The leg is involved. Male patient, age 18–29. This is a close-up image: 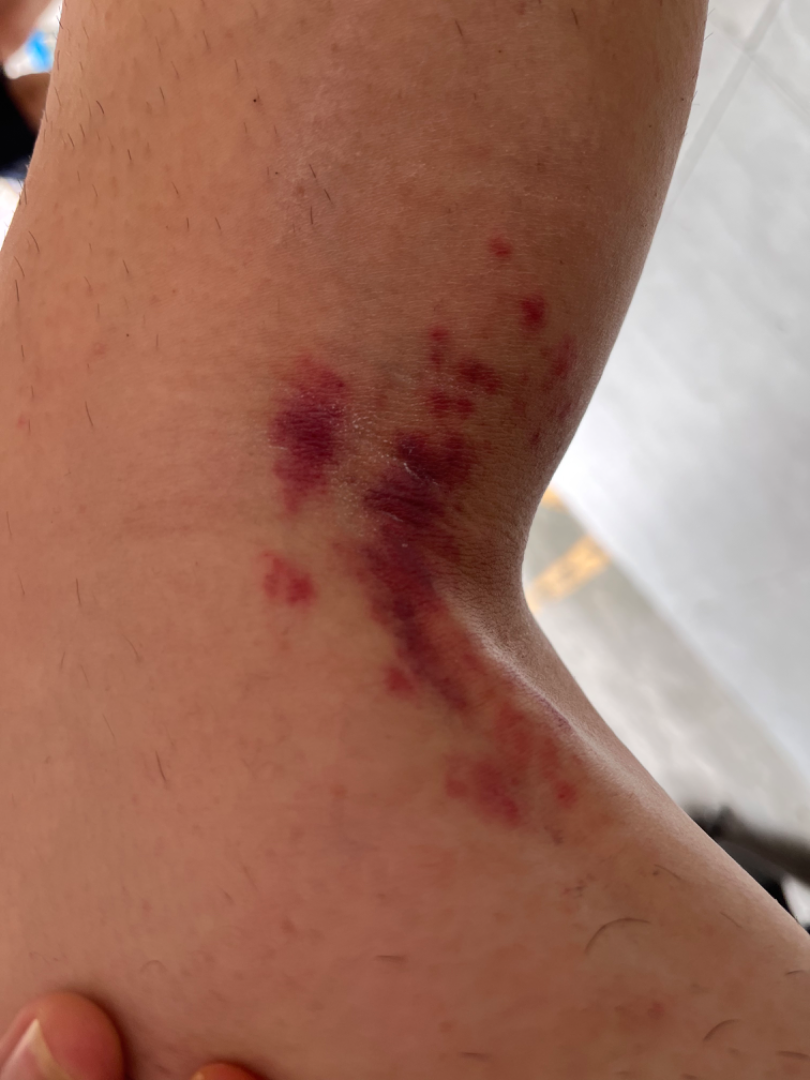Assessment: The reviewing dermatologist was unable to assign a differential diagnosis from the image.